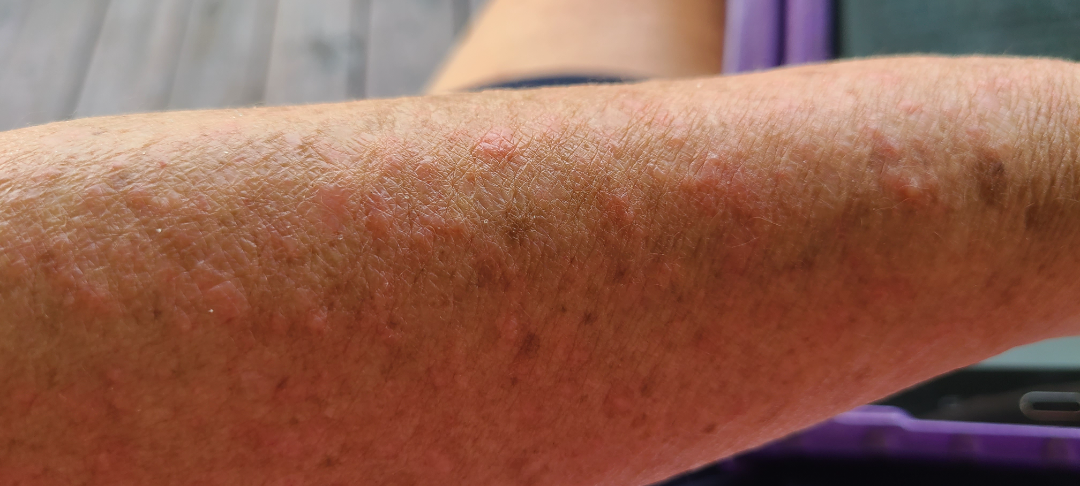  shot_type: close-up
  patient: female, age 60–69
  body_site: arm
  differential:
    tied_lead:
      - Photodermatitis
      - Urticaria